This image was taken at an angle · skin tone: Fitzpatrick skin type II:
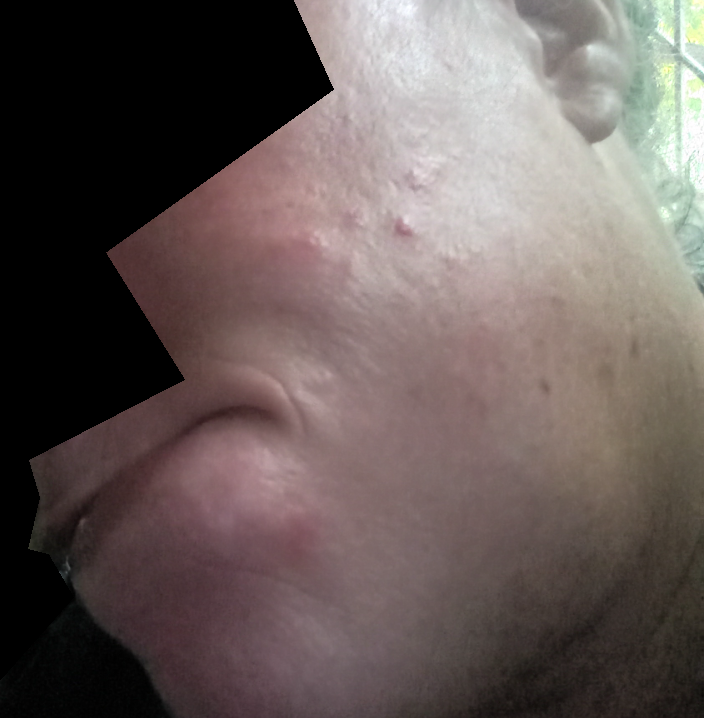  assessment: unable to determine